Reported duration is one to three months. The affected area is the front of the torso. Male patient, age 30–39. The patient considered this a rash. This is a close-up image. The lesion is described as flat. No relevant systemic symptoms. The patient did not report lesion symptoms: 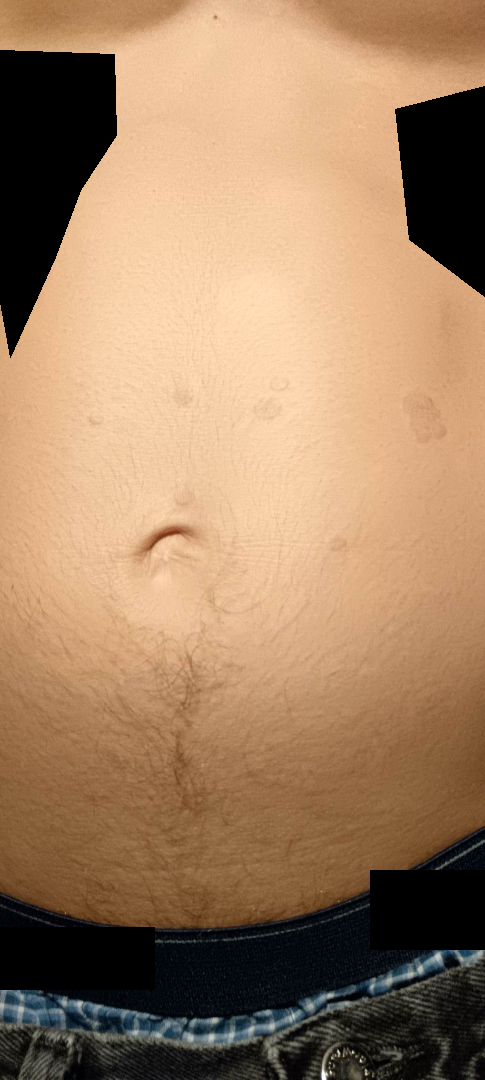The reviewing clinician's impression was: most likely Pityriasis rosea; an alternative is Eczema; with consideration of Lichen planus/lichenoid eruption.